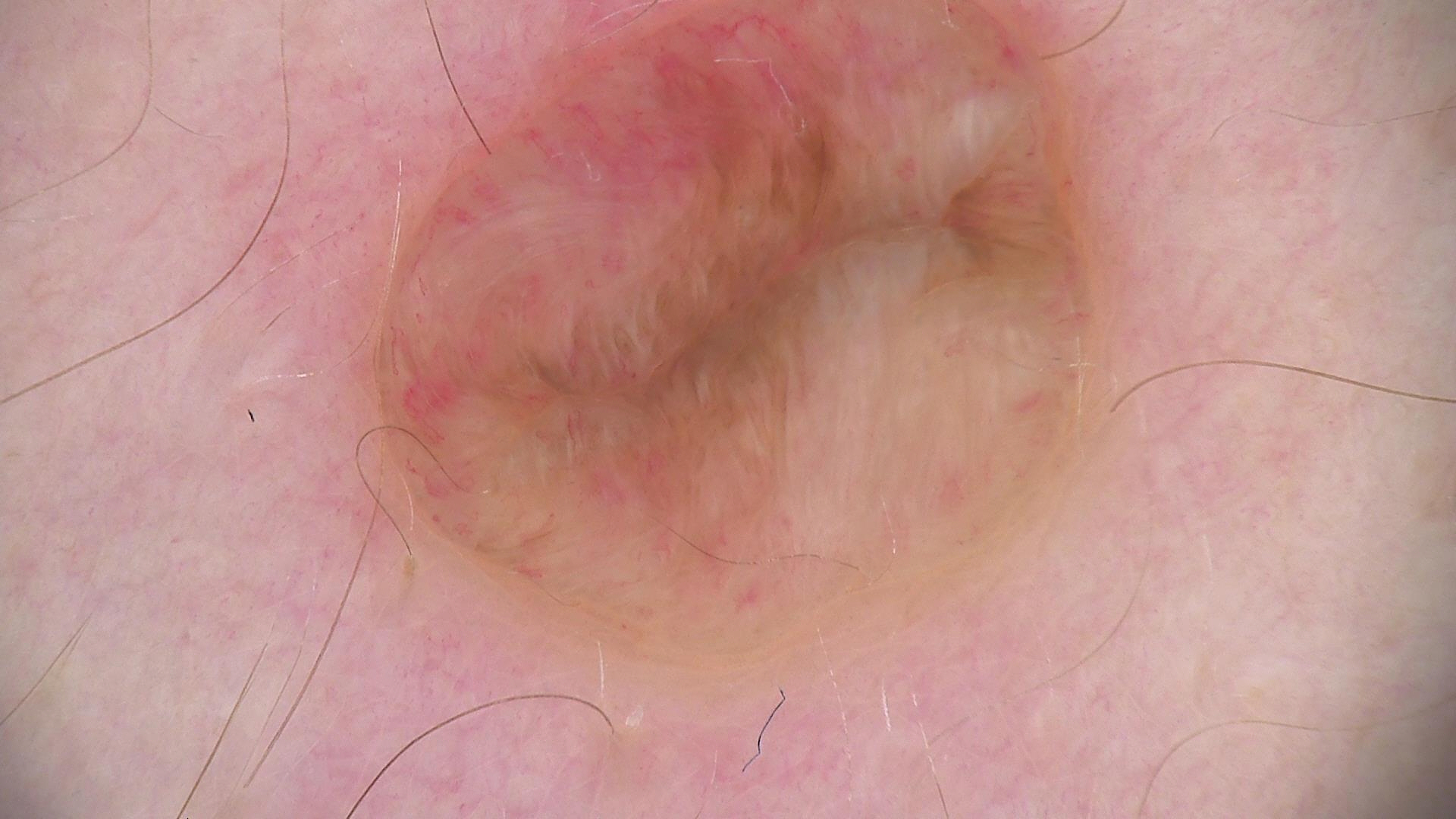Q: What was the diagnostic impression?
A: dermal nevus (expert consensus)